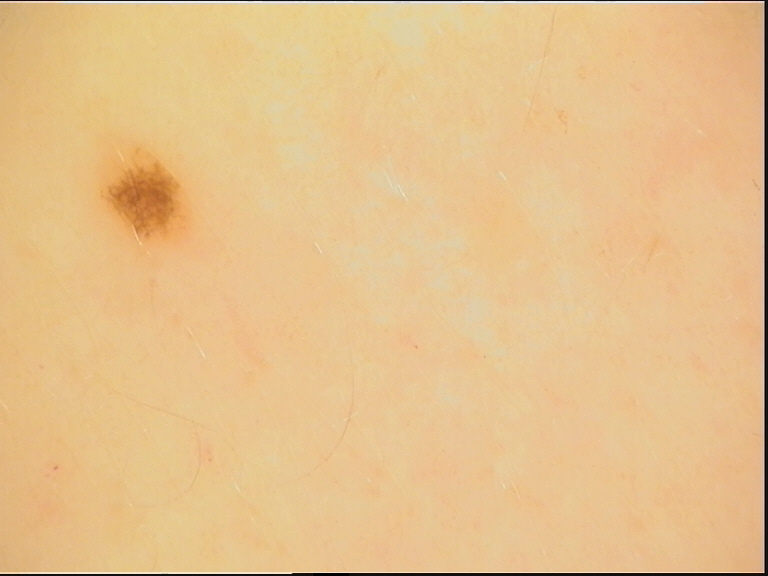diagnostic label=junctional nevus (expert consensus).